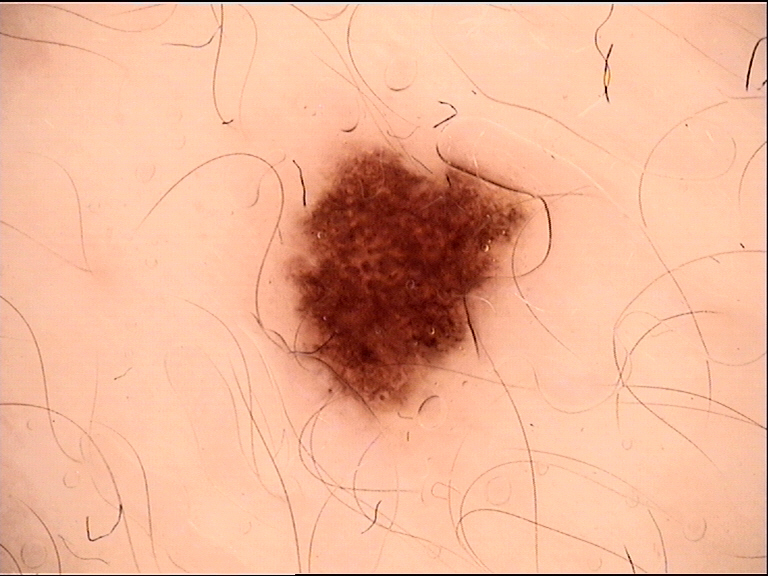Findings:
– imaging · dermatoscopy
– diagnosis · dysplastic junctional nevus (expert consensus)